A dermatoscopic image of a skin lesion.
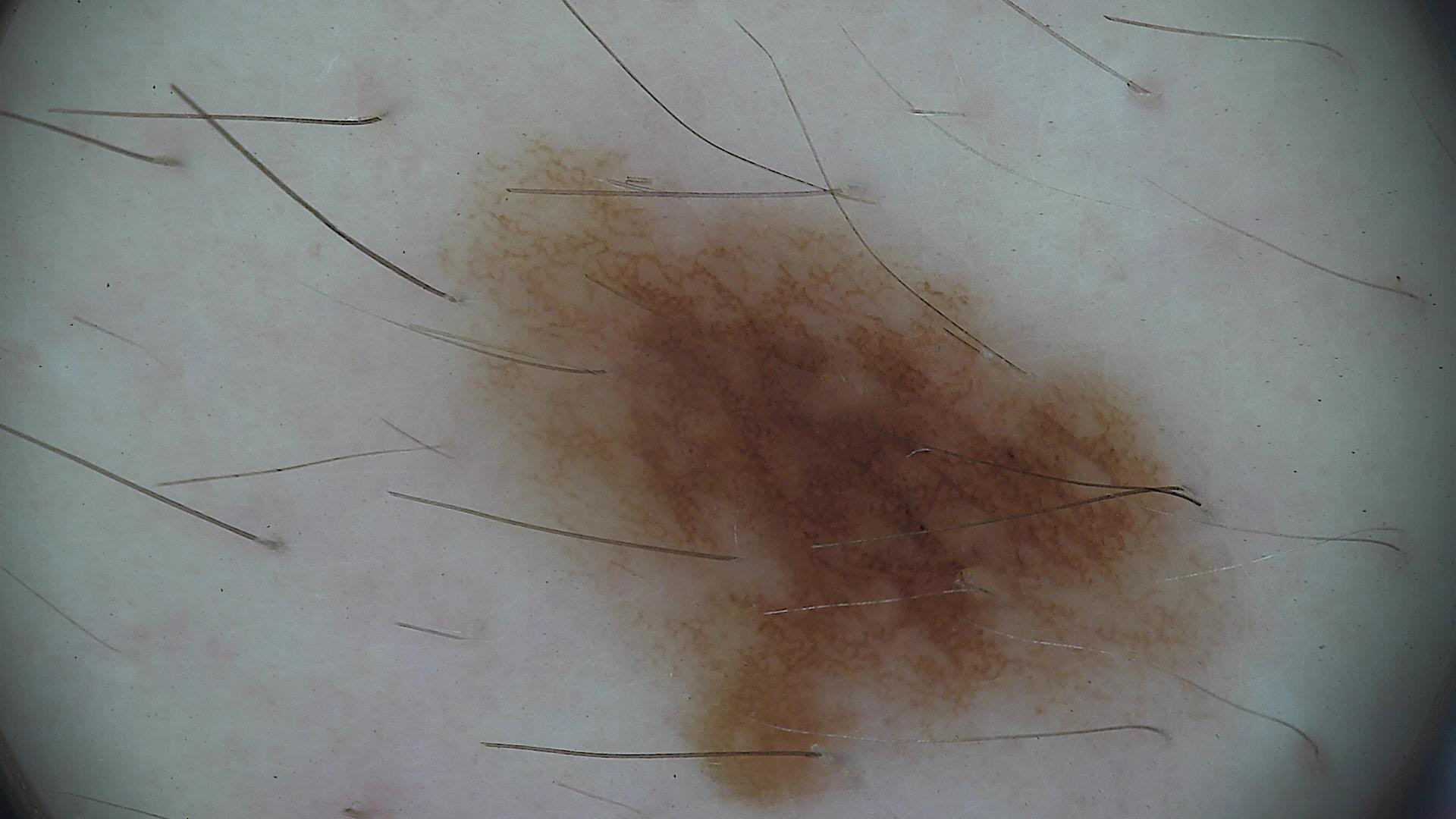Findings:
* label — dysplastic junctional nevus (expert consensus)